The lesion involves the leg, front of the torso, back of the hand and head or neck. This is a close-up image. Female patient, age 40–49 — 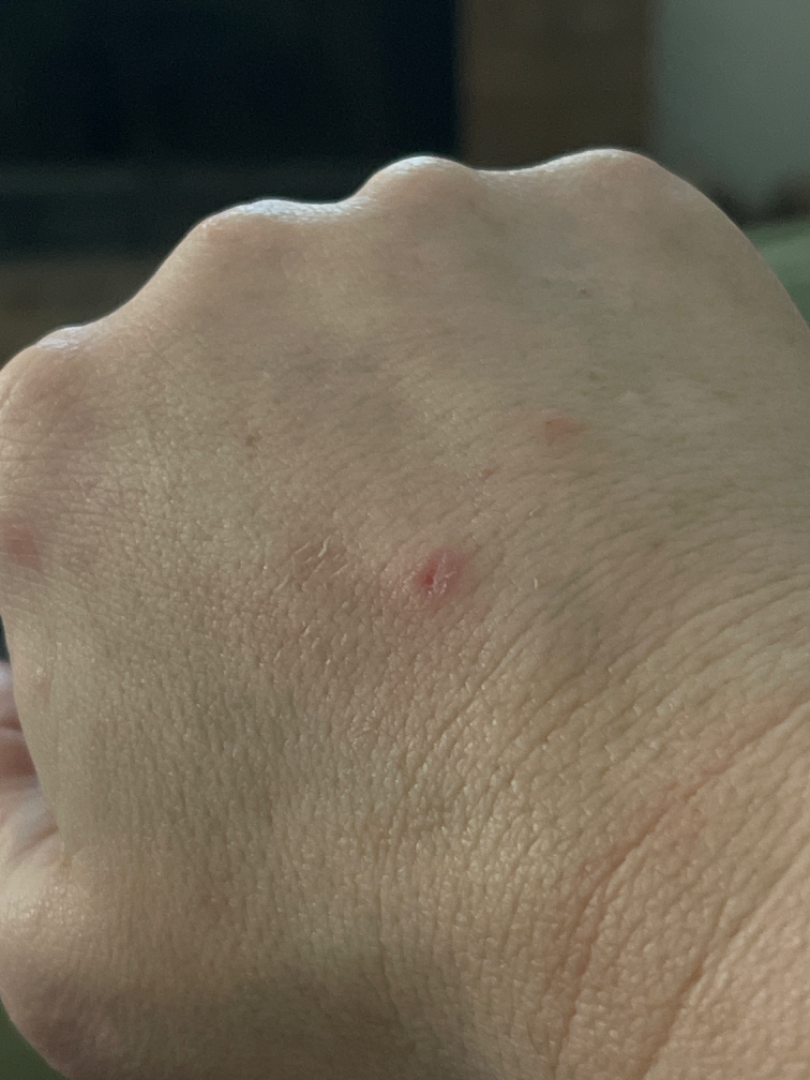Findings: Single-reviewer assessment: most likely Eczema; possibly Granuloma annulare.